Symptoms reported: itching · the leg and arm are involved · the patient described the issue as a rash · texture is reported as raised or bumpy · this is a close-up image — 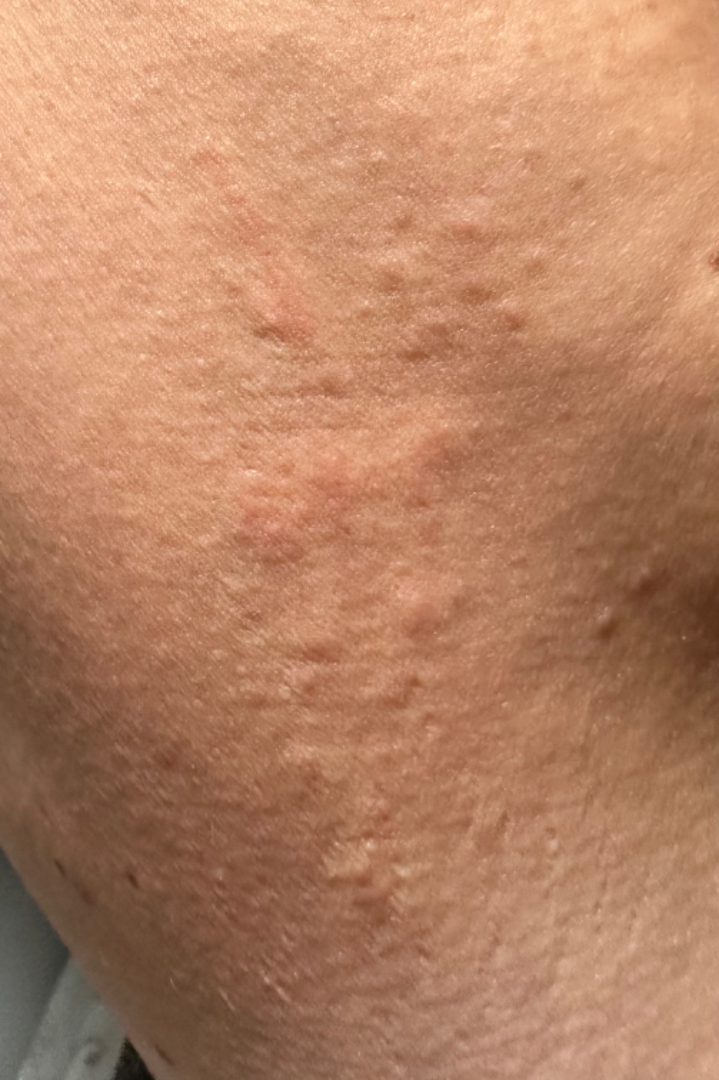assessment = indeterminate.